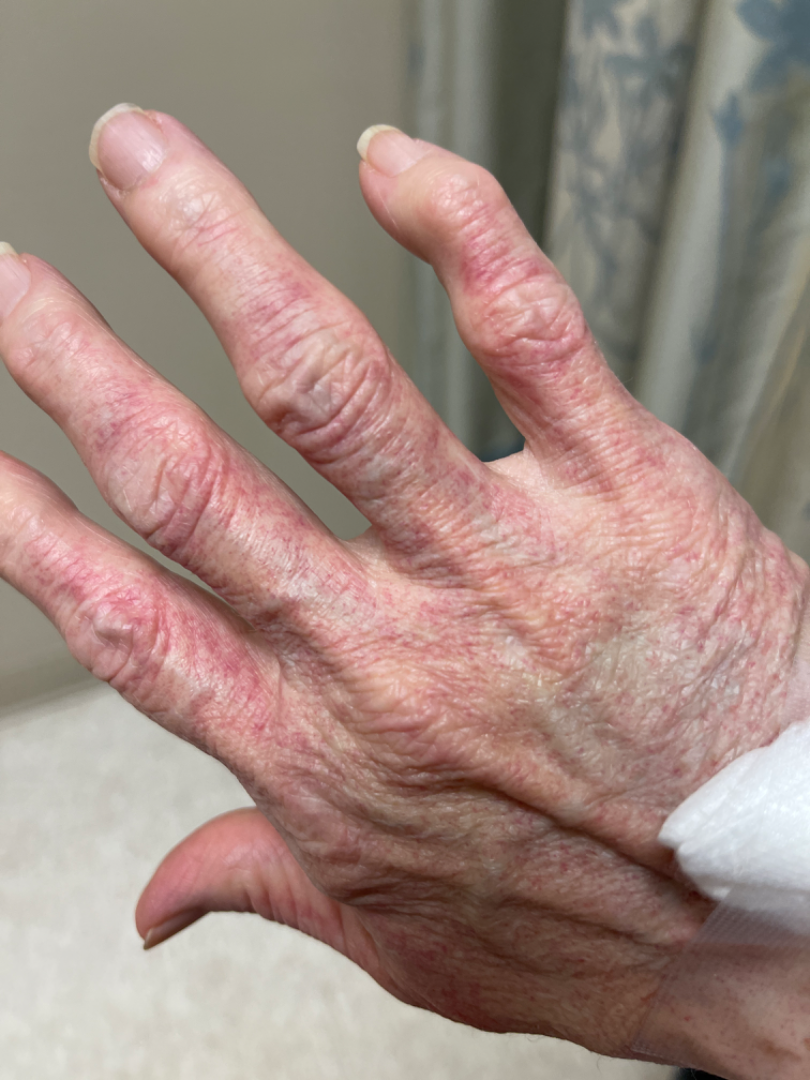{
  "assessment": "could not be assessed",
  "patient": "female, age 60–69",
  "shot_type": "at an angle",
  "body_site": "back of the hand"
}